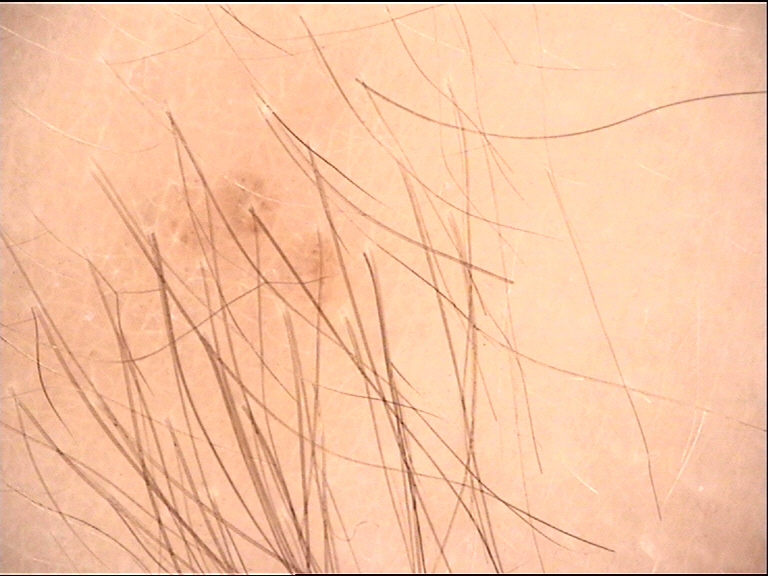image type — dermatoscopy; class — congenital compound nevus (expert consensus).